Female subject, age 18–29 · located on the leg and arm · the photograph is a close-up of the affected area — 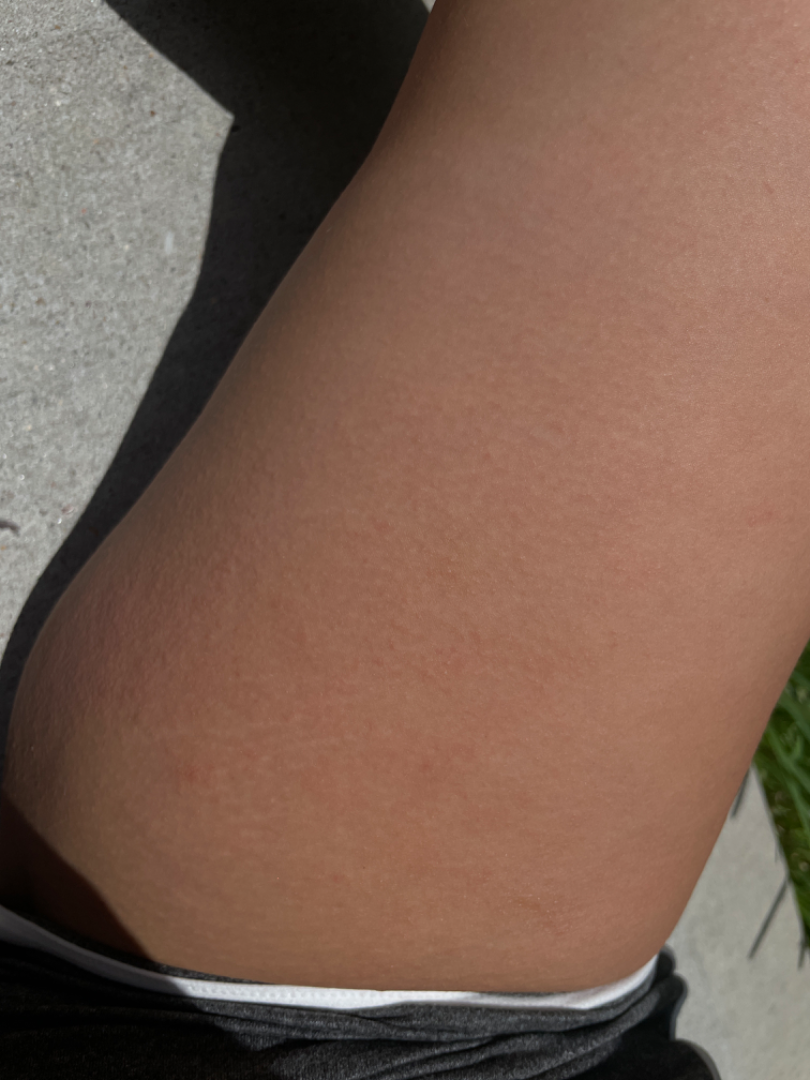assessment — no skin condition identified; self-categorized as — a rash; duration — less than one week.